This is a close-up image, located on the top or side of the foot — 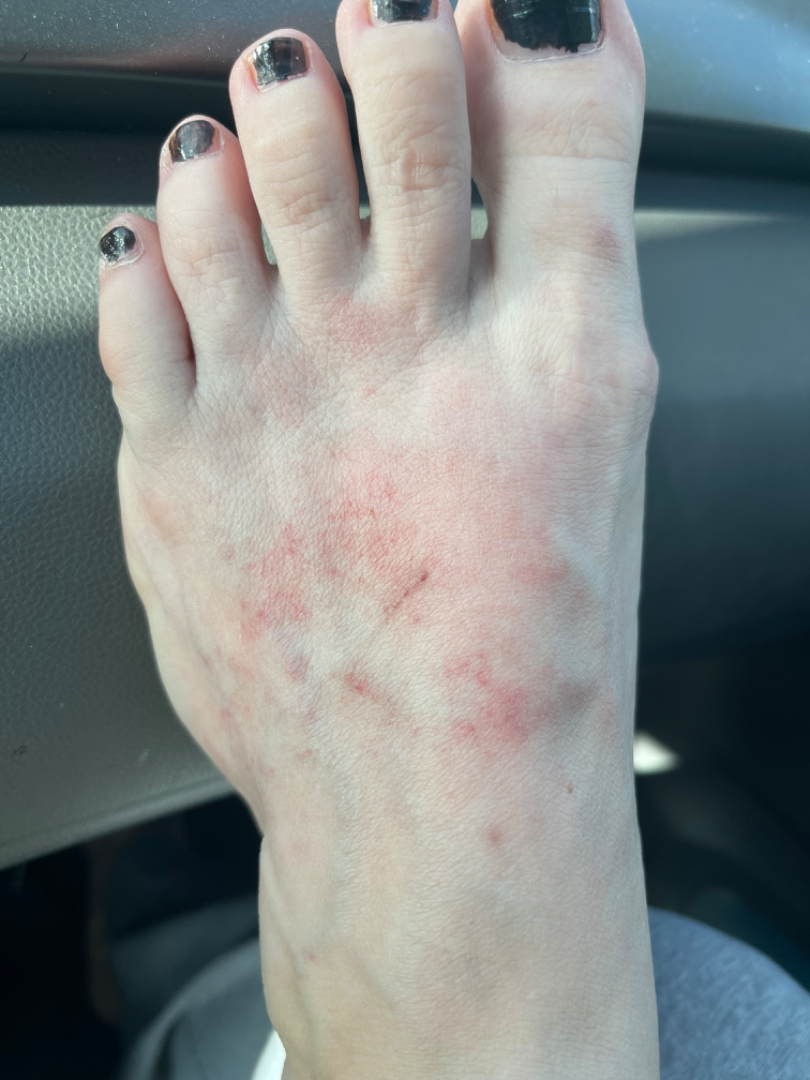No relevant systemic symptoms. The reviewing clinician's impression was: Eczema (considered); Allergic Contact Dermatitis (considered); Irritant Contact Dermatitis (considered).